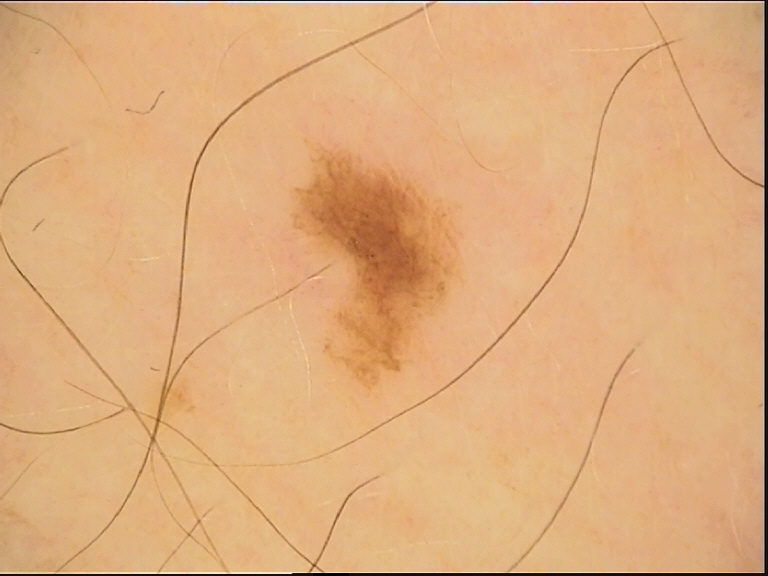Case: A dermoscopic photograph of a skin lesion. Conclusion: The diagnosis was a benign lesion — an acral dysplastic junctional nevus.